No associated systemic symptoms reported; the lesion is described as flat; skin tone: Fitzpatrick phototype III; the photograph is a close-up of the affected area; located on the top or side of the foot; present for less than one week:
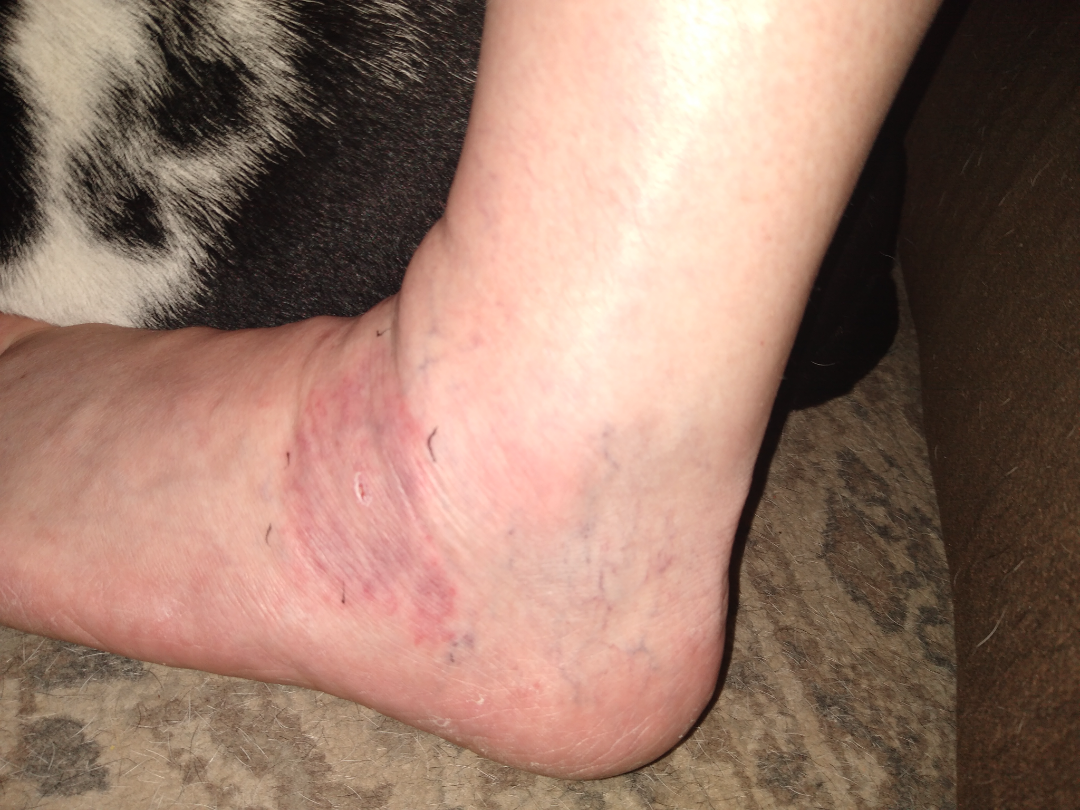Notes:
- diagnostic considerations · in keeping with Granuloma annulare